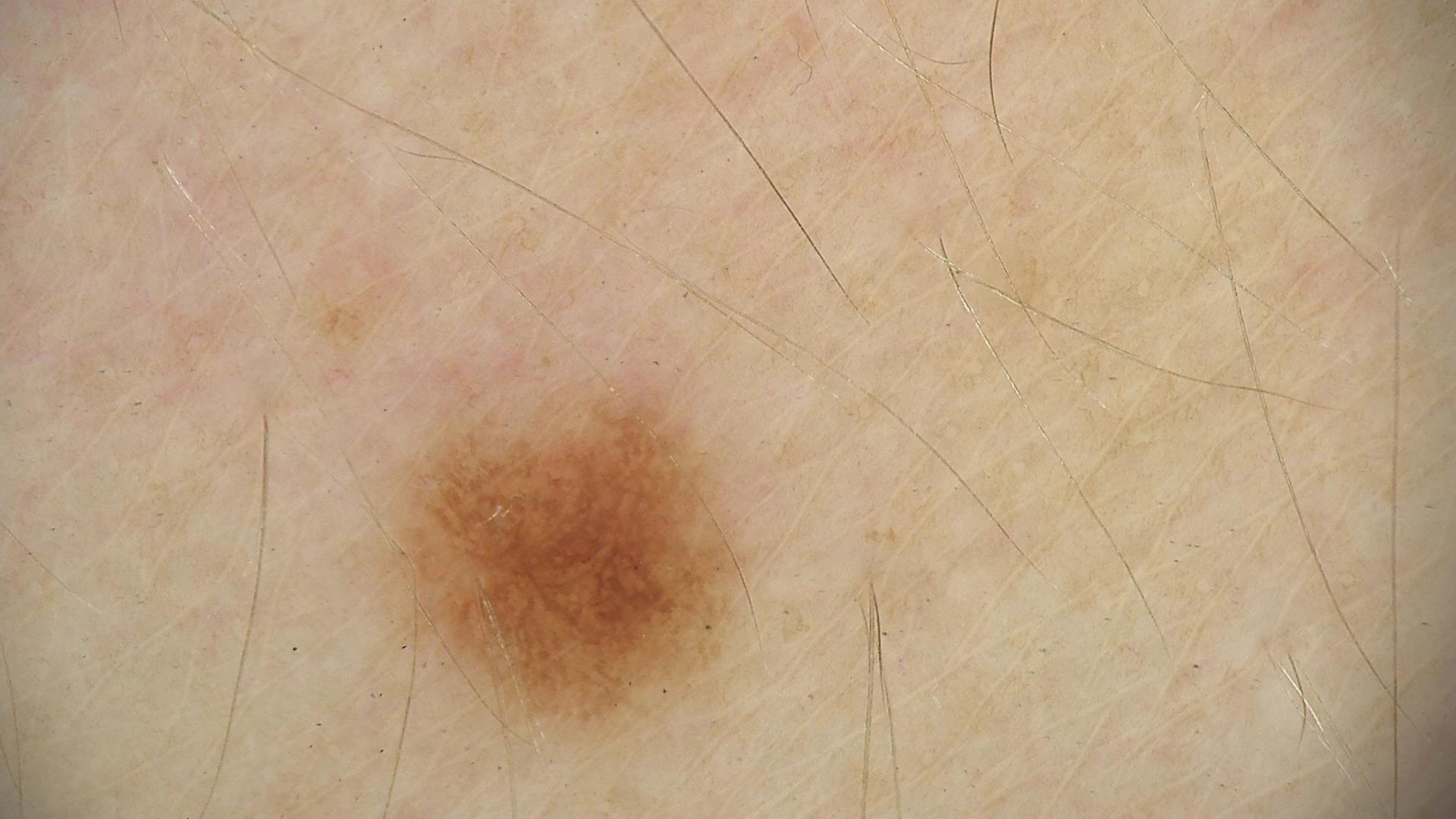Case: A skin lesion imaged with a dermatoscope. Impression: Diagnosed as a benign lesion — a dysplastic junctional nevus.